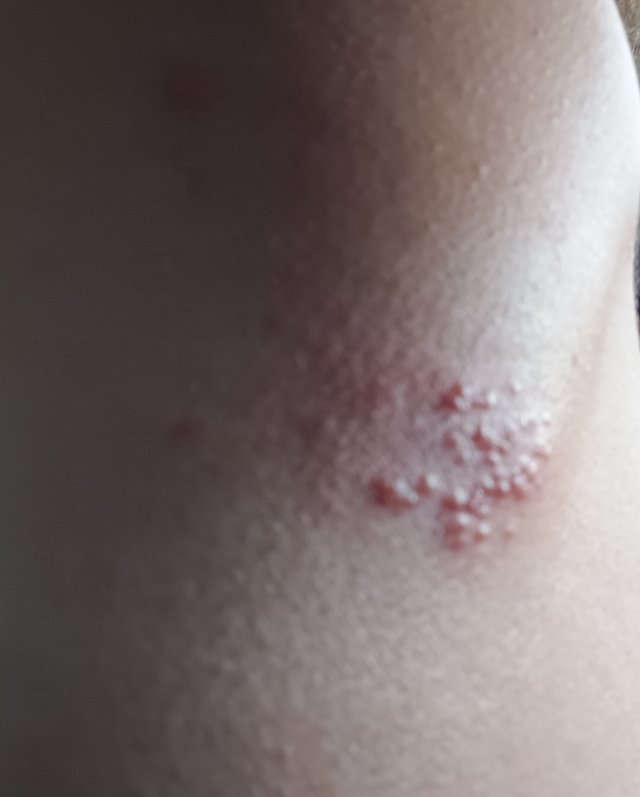Findings:
No differential diagnosis could be assigned on photographic review.